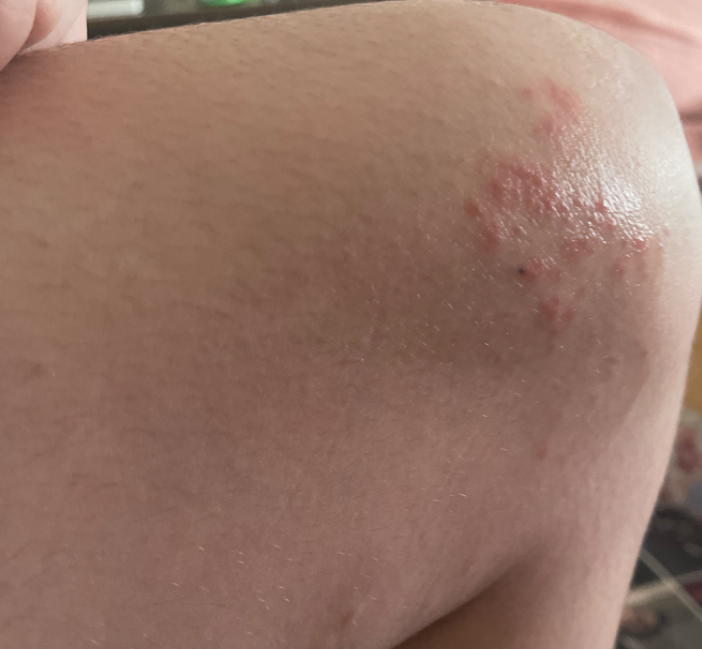<report>
<assessment>ungradable on photographic review</assessment>
</report>